Dermoscopy of a skin lesion.
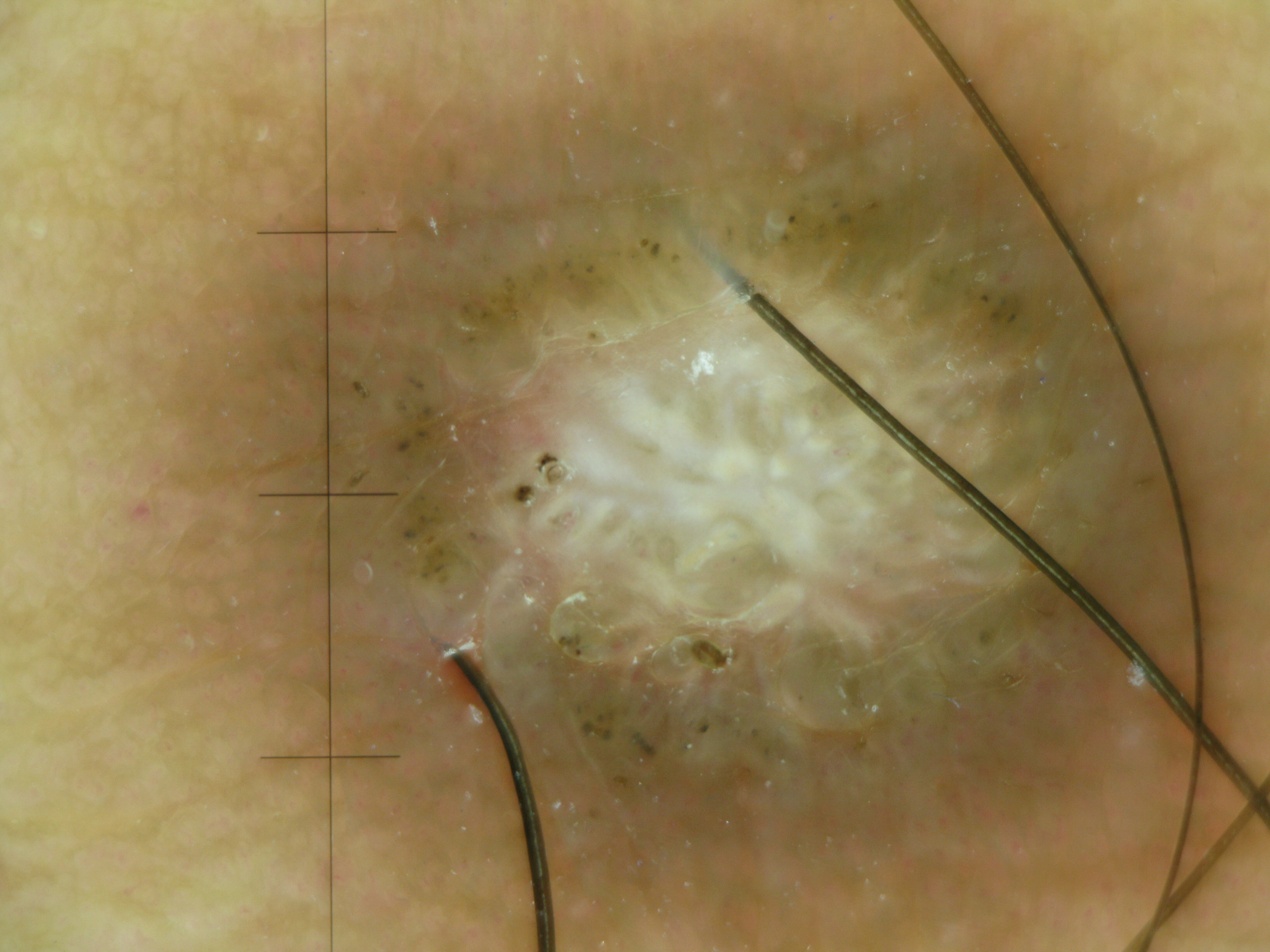* diagnostic label: dermatofibroma (expert consensus)